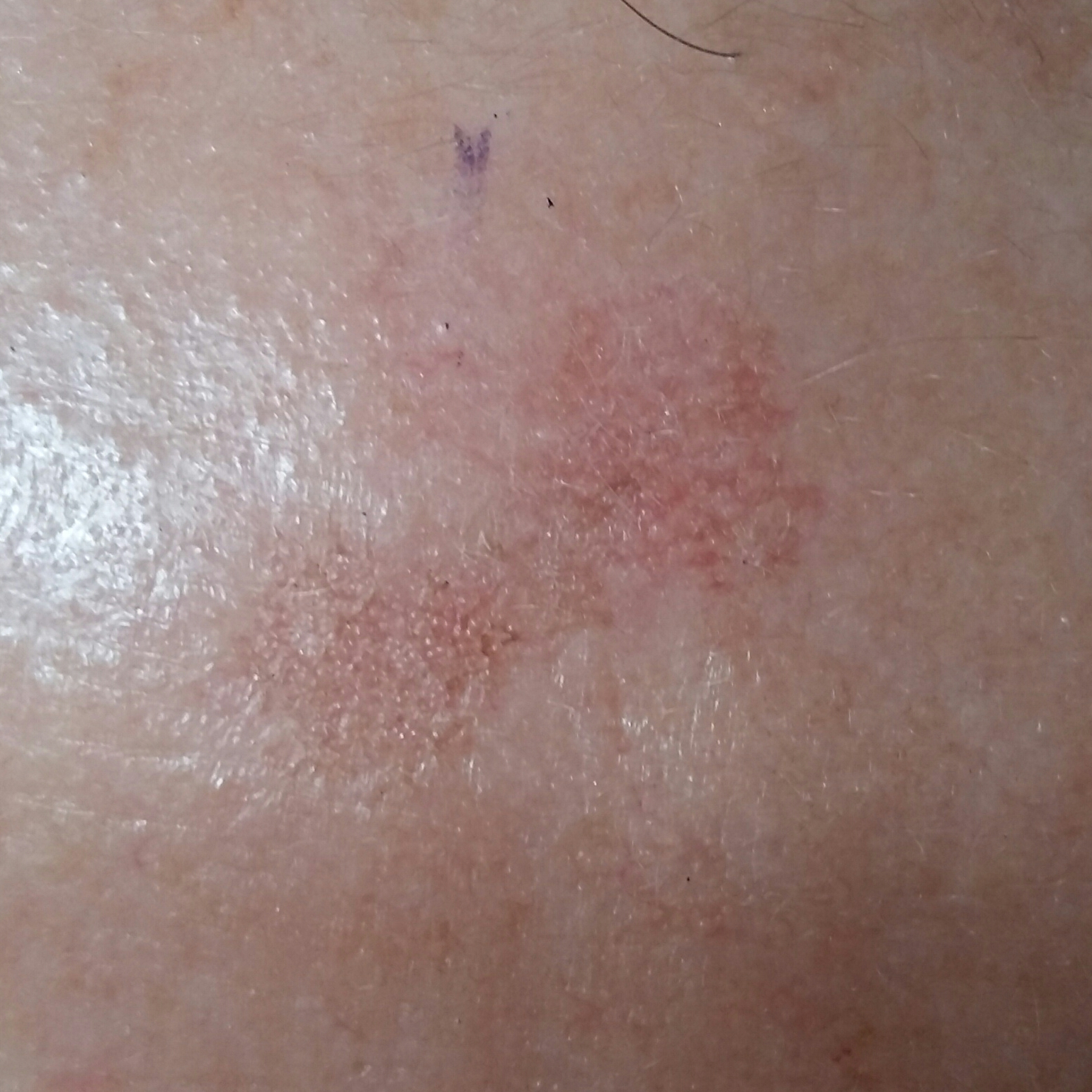diagnostic label: actinic keratosis (clinical consensus).